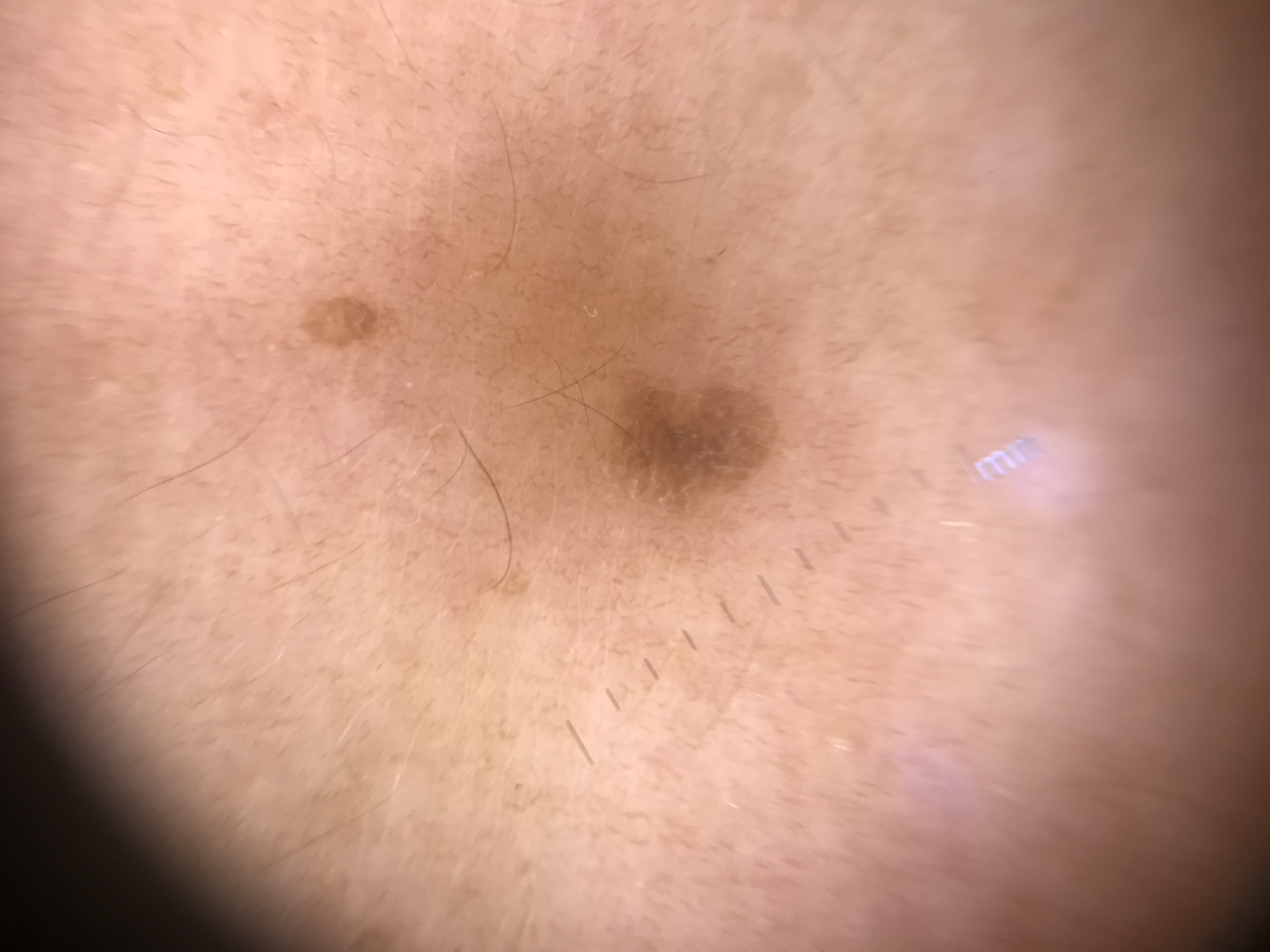Findings:
A dermoscopic close-up of a skin lesion. The architecture is that of a keratinocytic lesion.
Impression:
Consistent with a seborrheic keratosis.